A dermoscopy image of a single skin lesion.
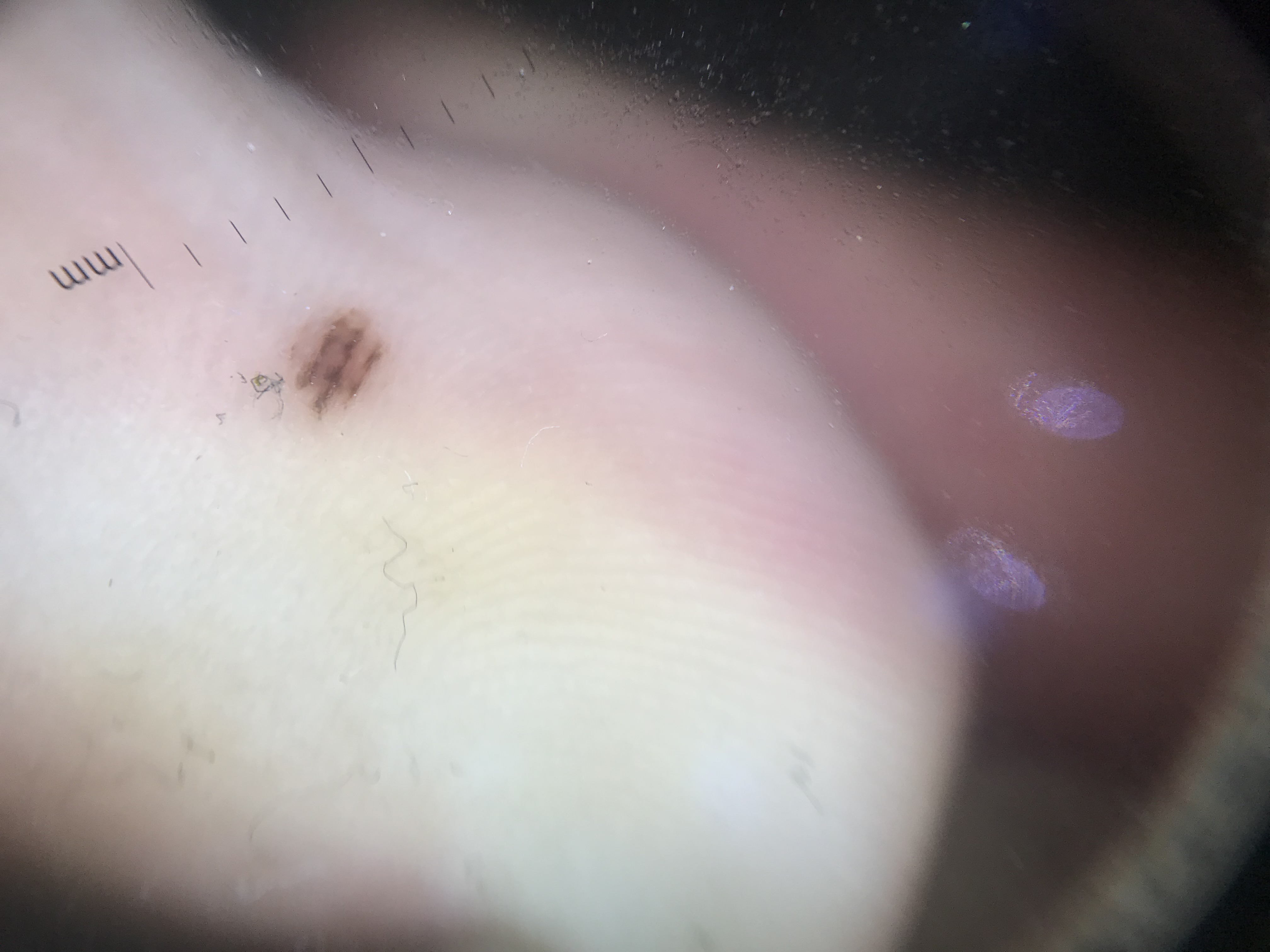Diagnosed as an acral dysplastic junctional nevus.